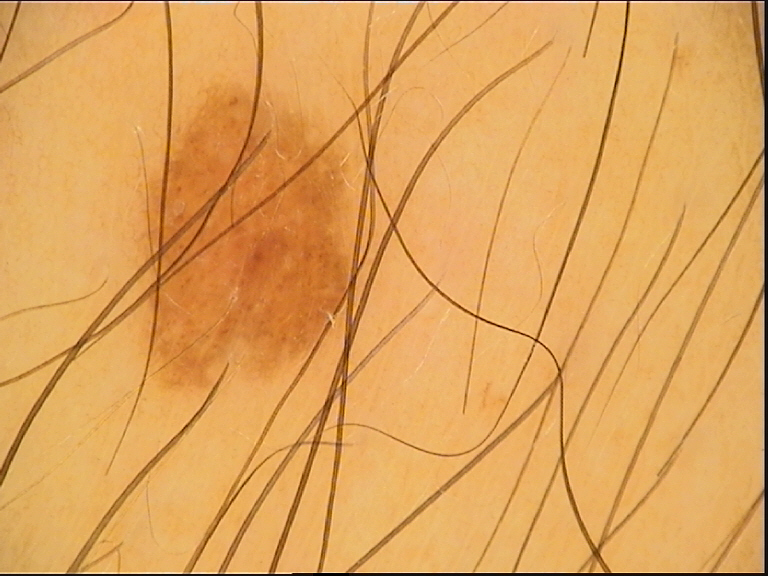Findings:
– label: dysplastic junctional nevus (expert consensus)